A female subject roughly 40 years of age; an overview clinical photograph of a skin lesion; the patient was assessed as Fitzpatrick phototype III.
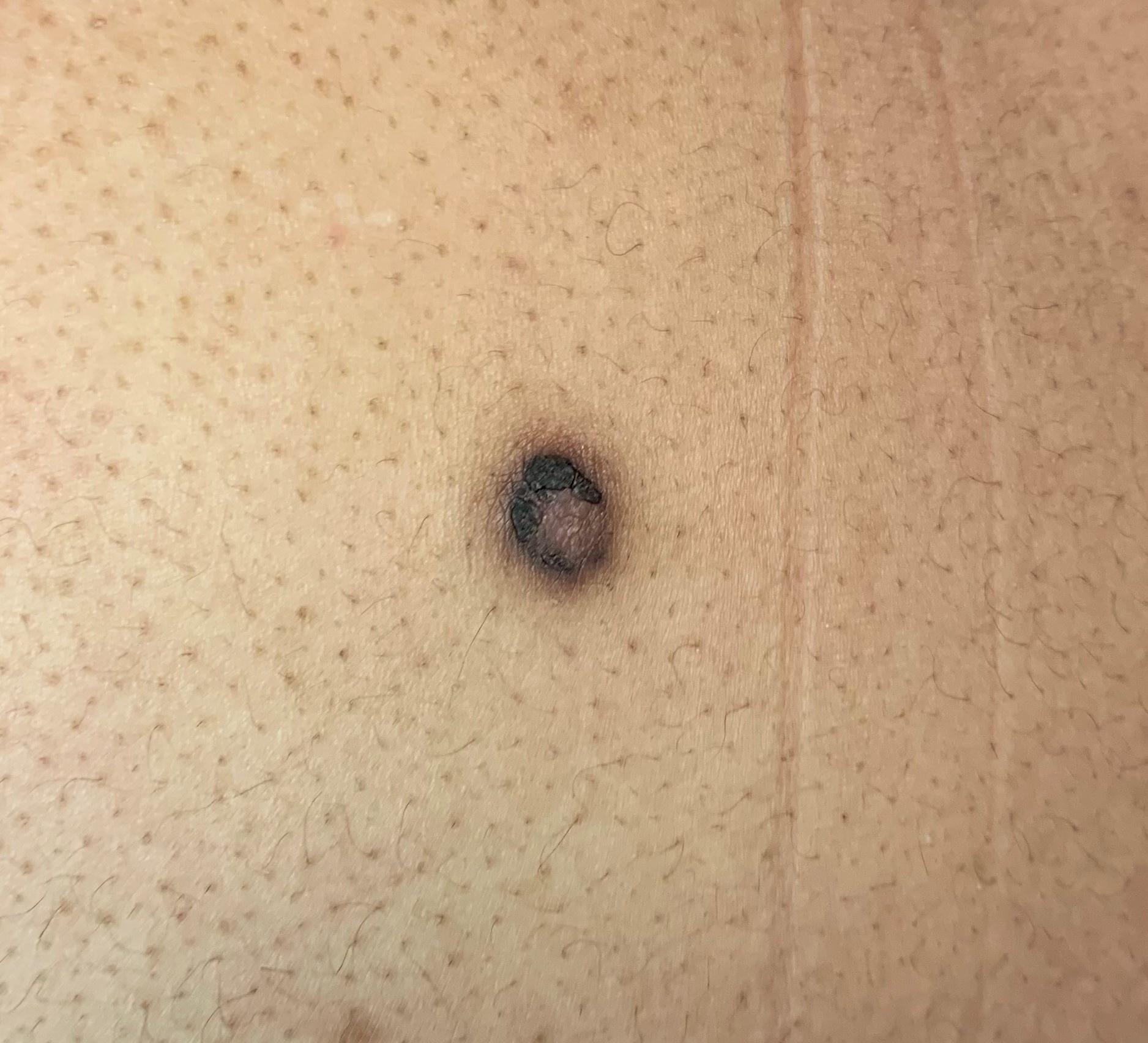| key | value |
|---|---|
| location | a lower extremity |
| pathology | Dermatofibroma (biopsy-proven) |